A skin lesion imaged with a dermatoscope.
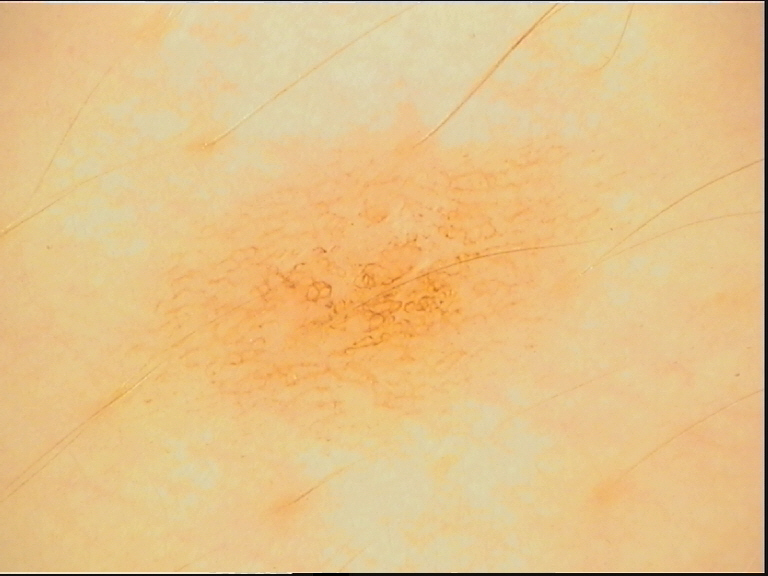<dermoscopy>
<diagnosis>
<name>dysplastic junctional nevus</name>
<code>jd</code>
<malignancy>benign</malignancy>
<super_class>melanocytic</super_class>
<confirmation>expert consensus</confirmation>
</diagnosis>
</dermoscopy>